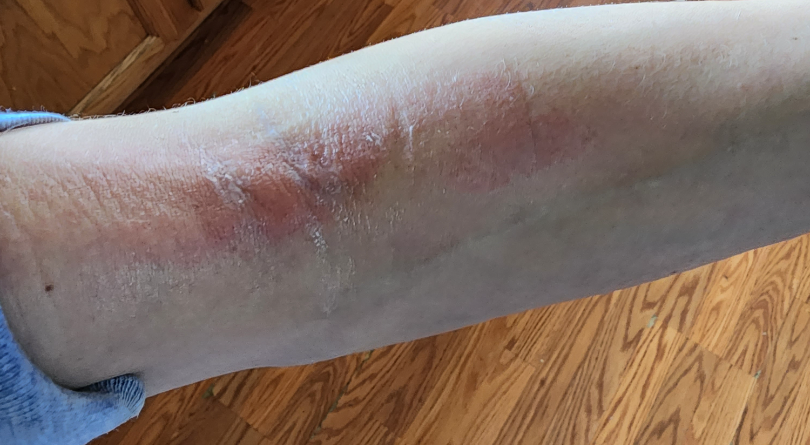The reviewing dermatologist was unable to assign a differential diagnosis from the image.
Located on the arm.
This image was taken at a distance.